A male patient aged approximately 45, a dermatoscopic image of a skin lesion.
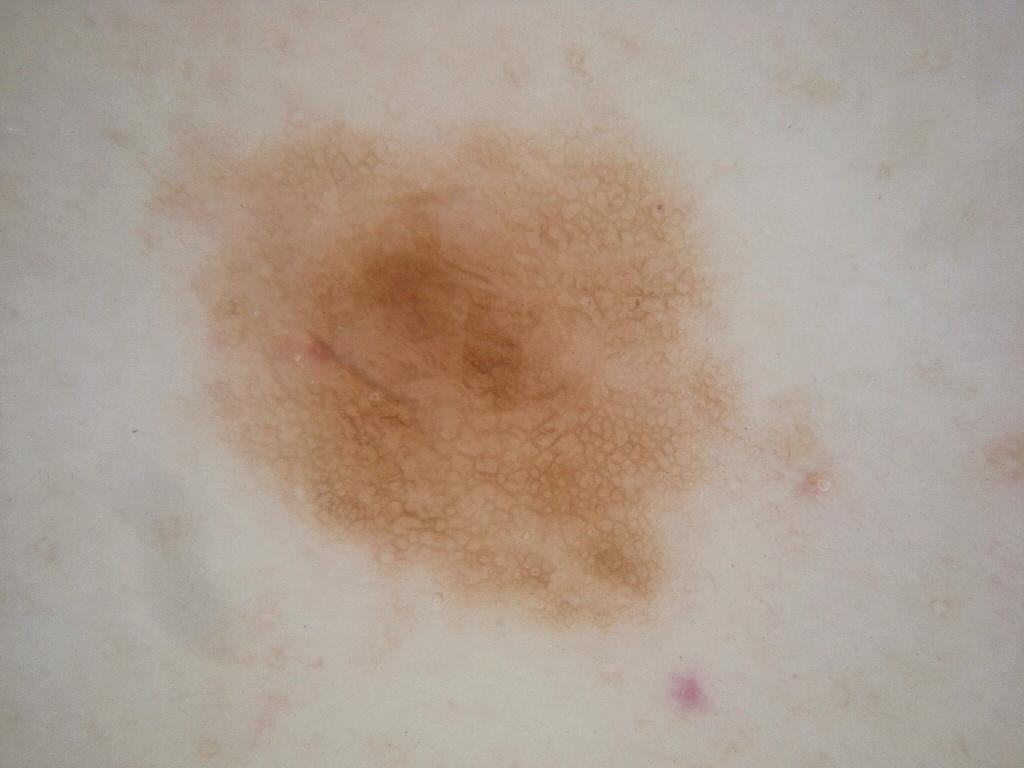A large lesion occupying much of the field.
Dermoscopic assessment notes pigment network, with no globules, negative network, milia-like cysts, or streaks.
The lesion is bounded by x1=123, y1=85, x2=848, y2=654.
Expert review diagnosed this as a melanocytic nevus, a benign lesion.